A dermatoscopic image of a skin lesion.
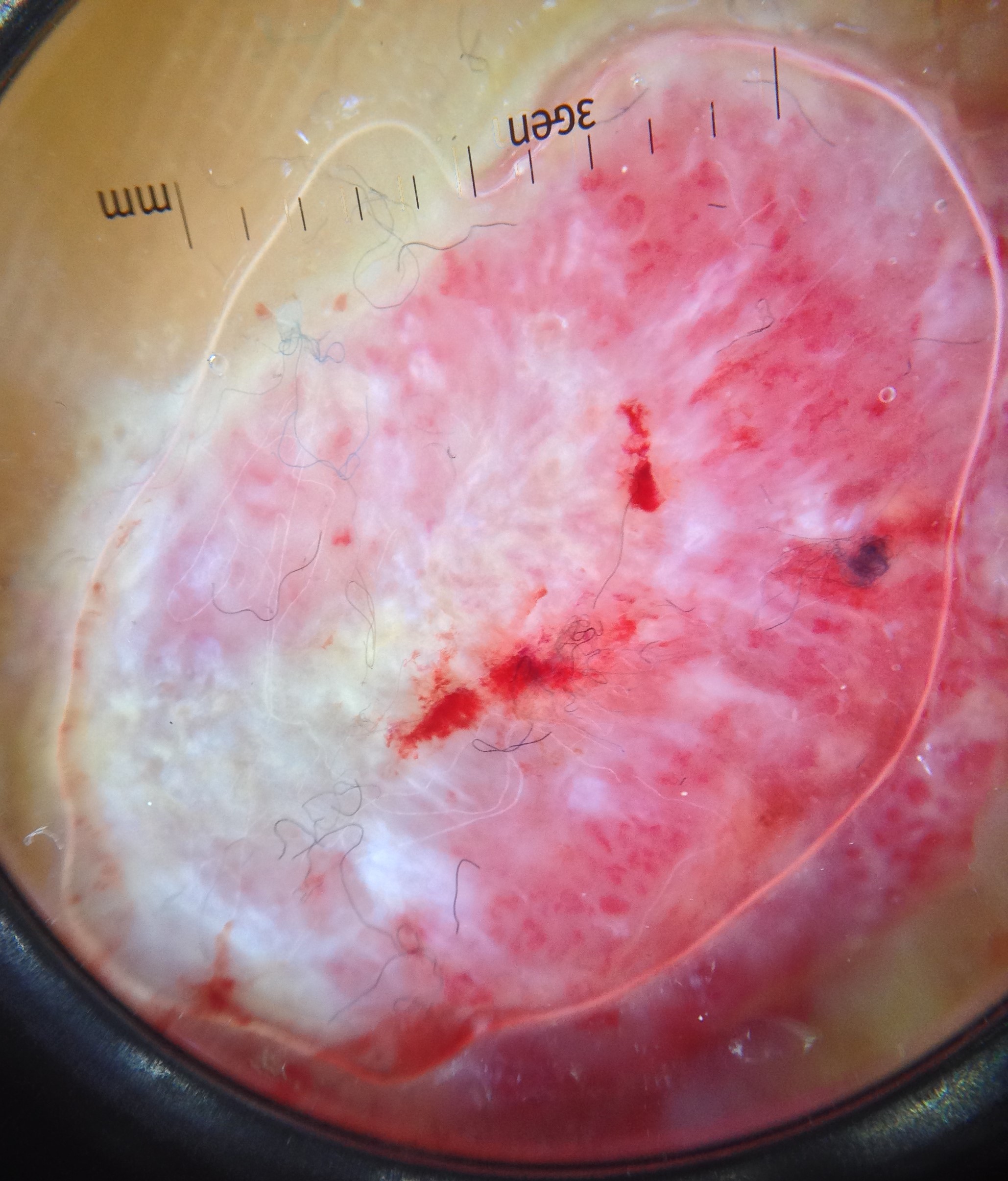Q: What is the diagnosis?
A: acral nodular melanoma (biopsy-proven)